A skin lesion imaged with a dermatoscope, a male patient in their mid-60s — 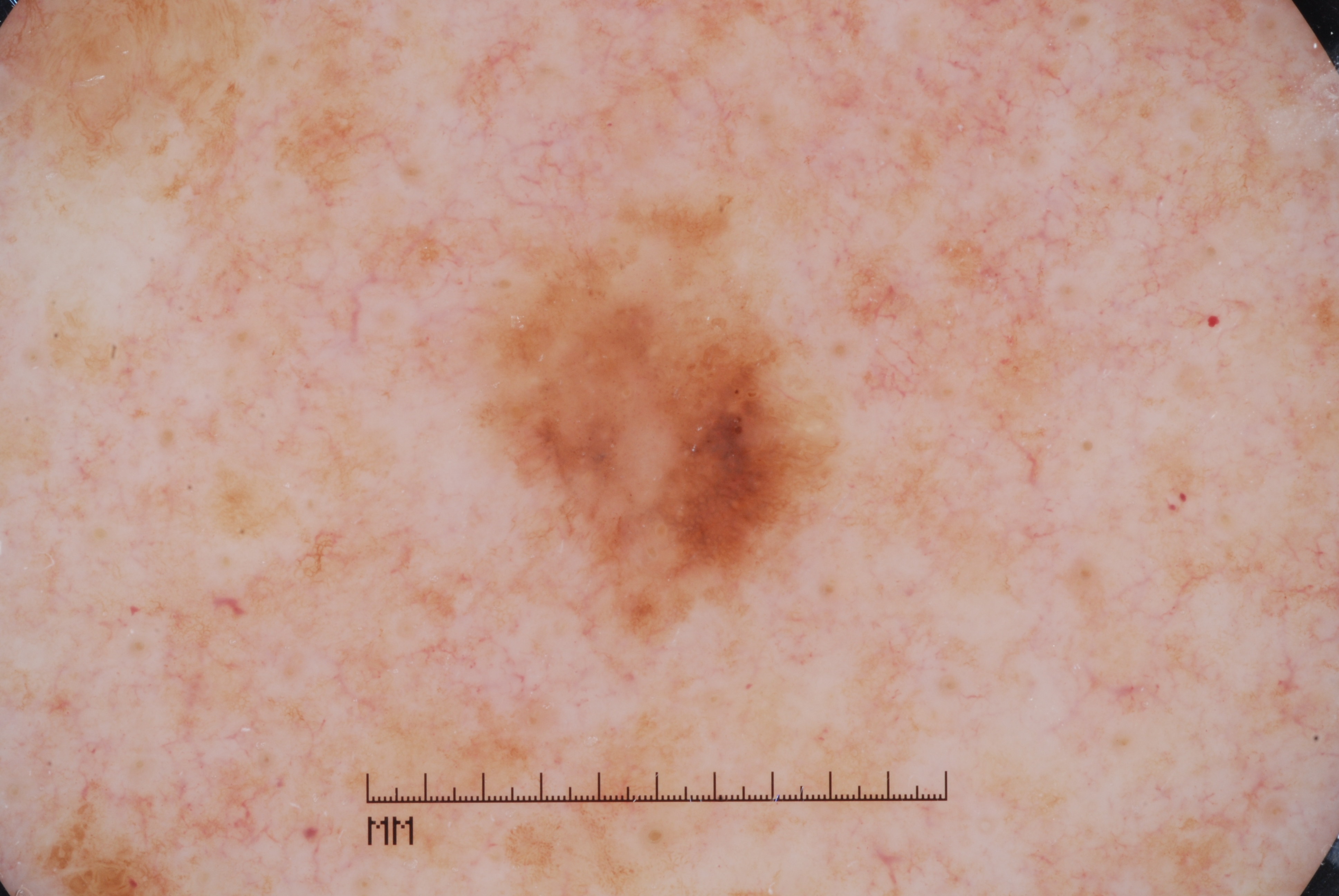A small lesion occupying a minor part of the field. Dermoscopically, the lesion shows pigment network and milia-like cysts, with no streaks or negative network. Lesion location: (491, 253, 826, 623). Histopathology confirmed a melanoma, a malignant skin lesion.